Dermoscopy of a skin lesion:
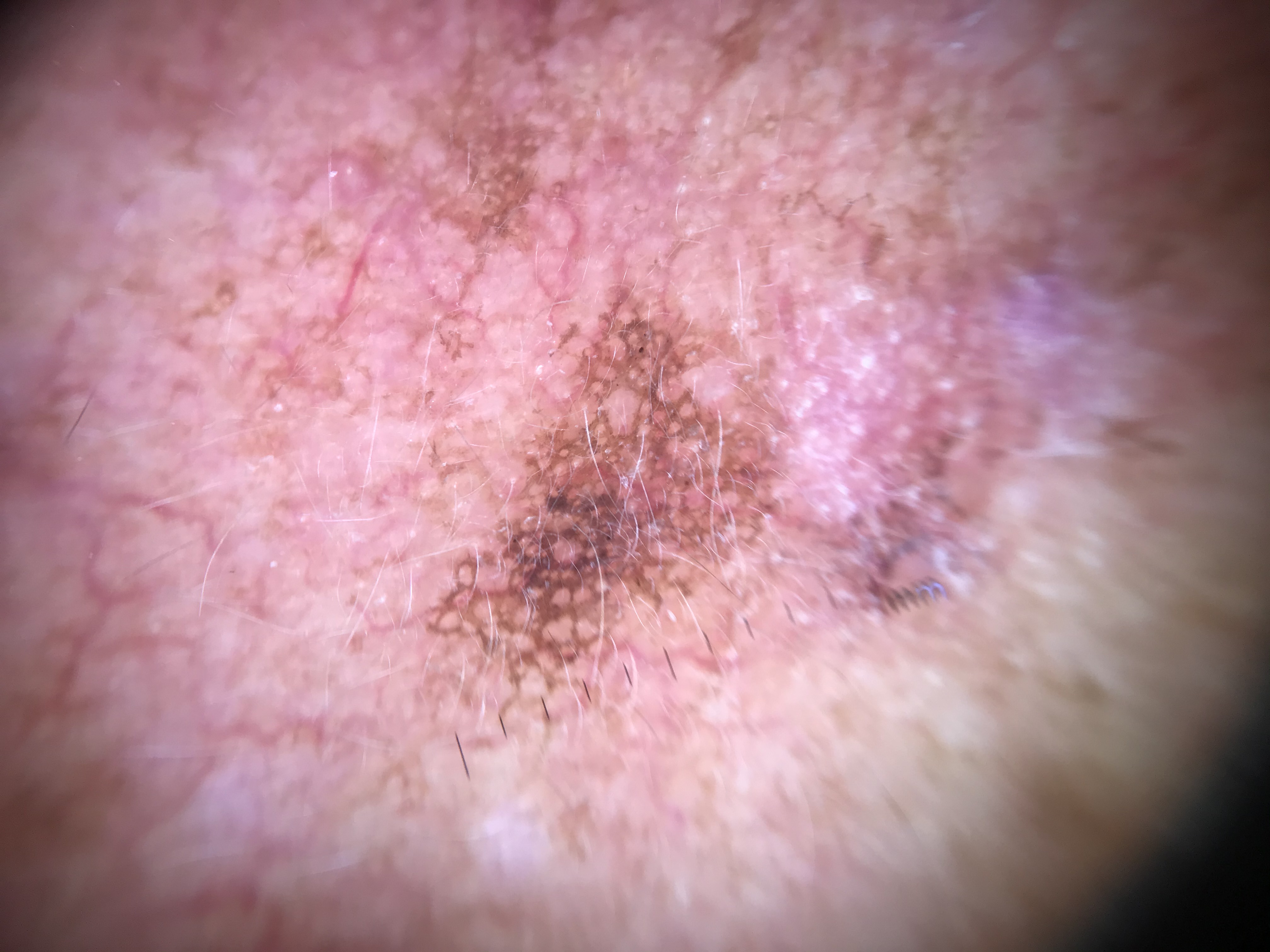| key | value |
|---|---|
| label | actinic keratosis (expert consensus) |